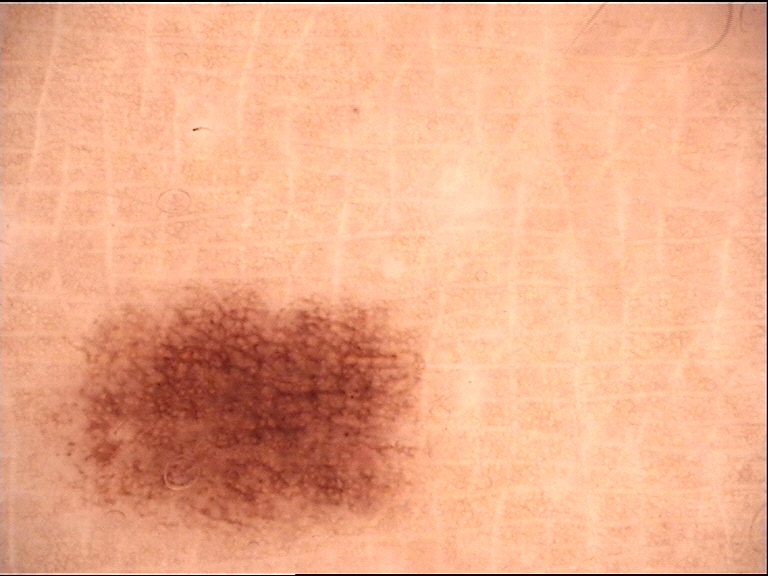{
  "diagnosis": {
    "name": "dysplastic junctional nevus",
    "code": "jd",
    "malignancy": "benign",
    "super_class": "melanocytic",
    "confirmation": "expert consensus"
  }
}